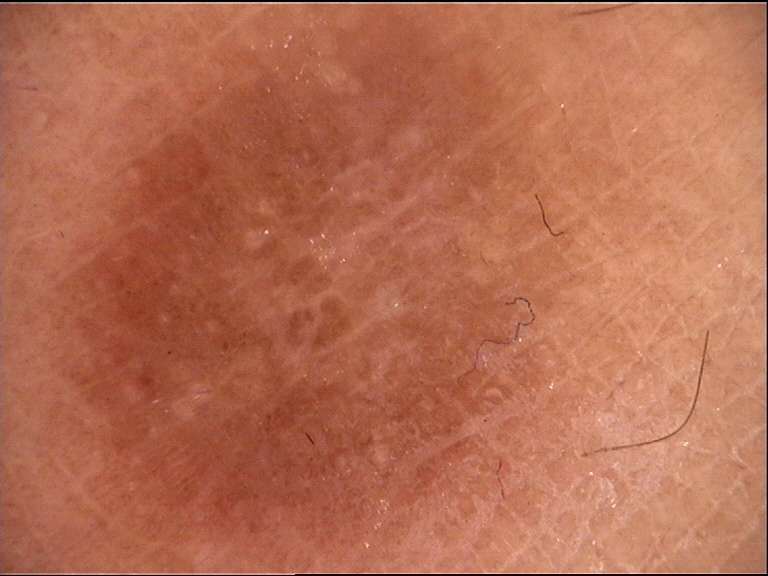Findings:
• image type: dermatoscopy
• diagnosis: dermatofibroma (expert consensus)